A dermoscopic image of a skin lesion: 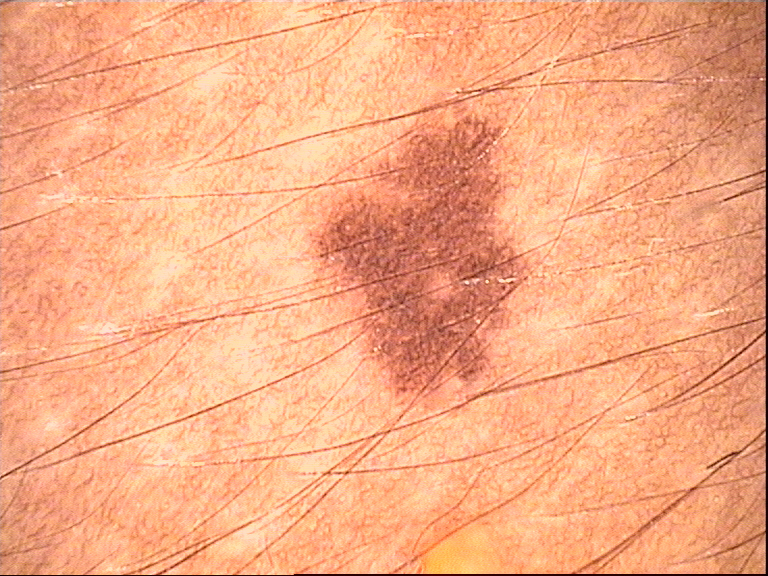{
  "diagnosis": {
    "name": "dysplastic junctional nevus",
    "code": "jd",
    "malignancy": "benign",
    "super_class": "melanocytic",
    "confirmation": "expert consensus"
  }
}